A male subject aged 18 to 22 · the patient was assessed as Fitzpatrick phototype II · a dermoscopic image of a skin lesion · per the chart, a first-degree relative with melanoma — 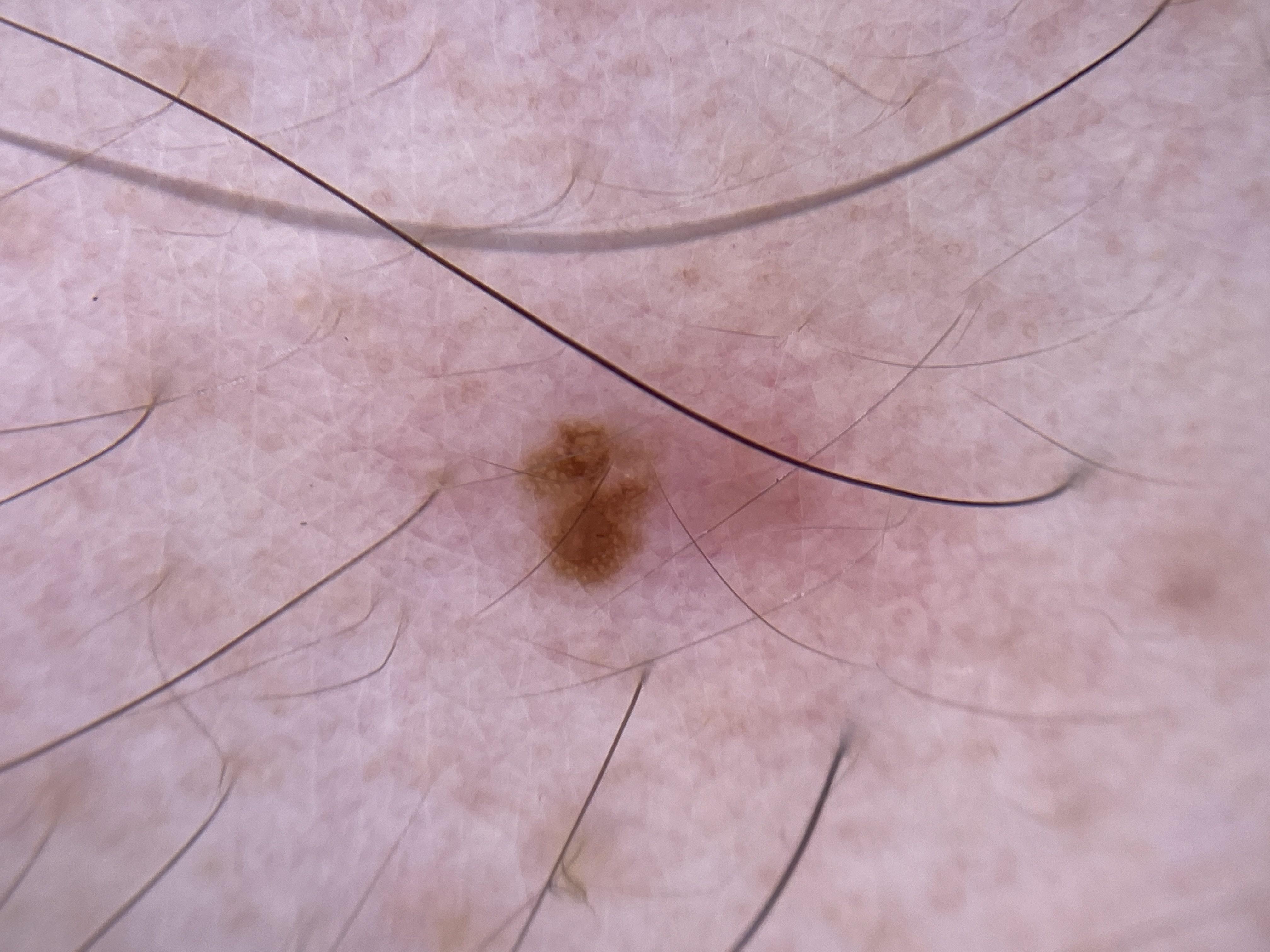Case:
* site: the trunk
* assessment: Nevus